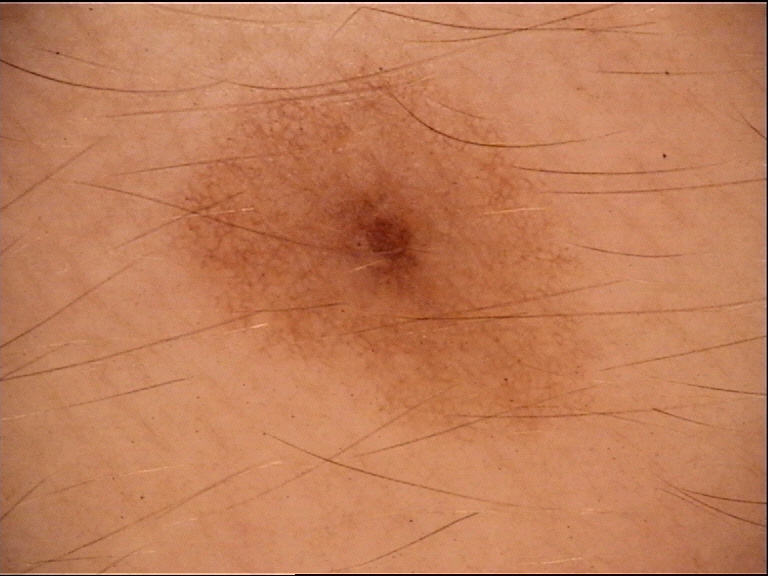| field | value |
|---|---|
| assessment | dysplastic junctional nevus (expert consensus) |